The subject is a female aged approximately 45 · dermoscopy of a skin lesion:
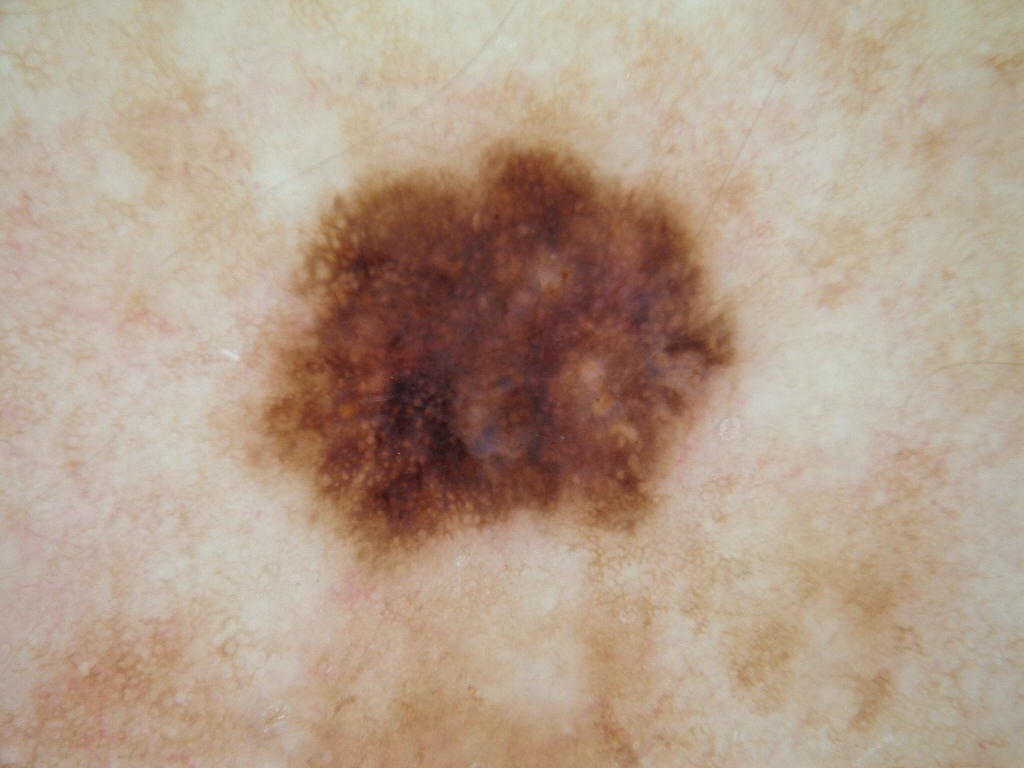Image and clinical context: Dermoscopic review identifies pigment network, with no milia-like cysts, streaks, globules, or negative network. With coordinates (x1, y1, x2, y2), the visible lesion spans 245/134/738/594. The lesion covers approximately 20% of the dermoscopic field. Conclusion: The biopsy diagnosis was a melanoma.